A dermoscopic close-up of a skin lesion.
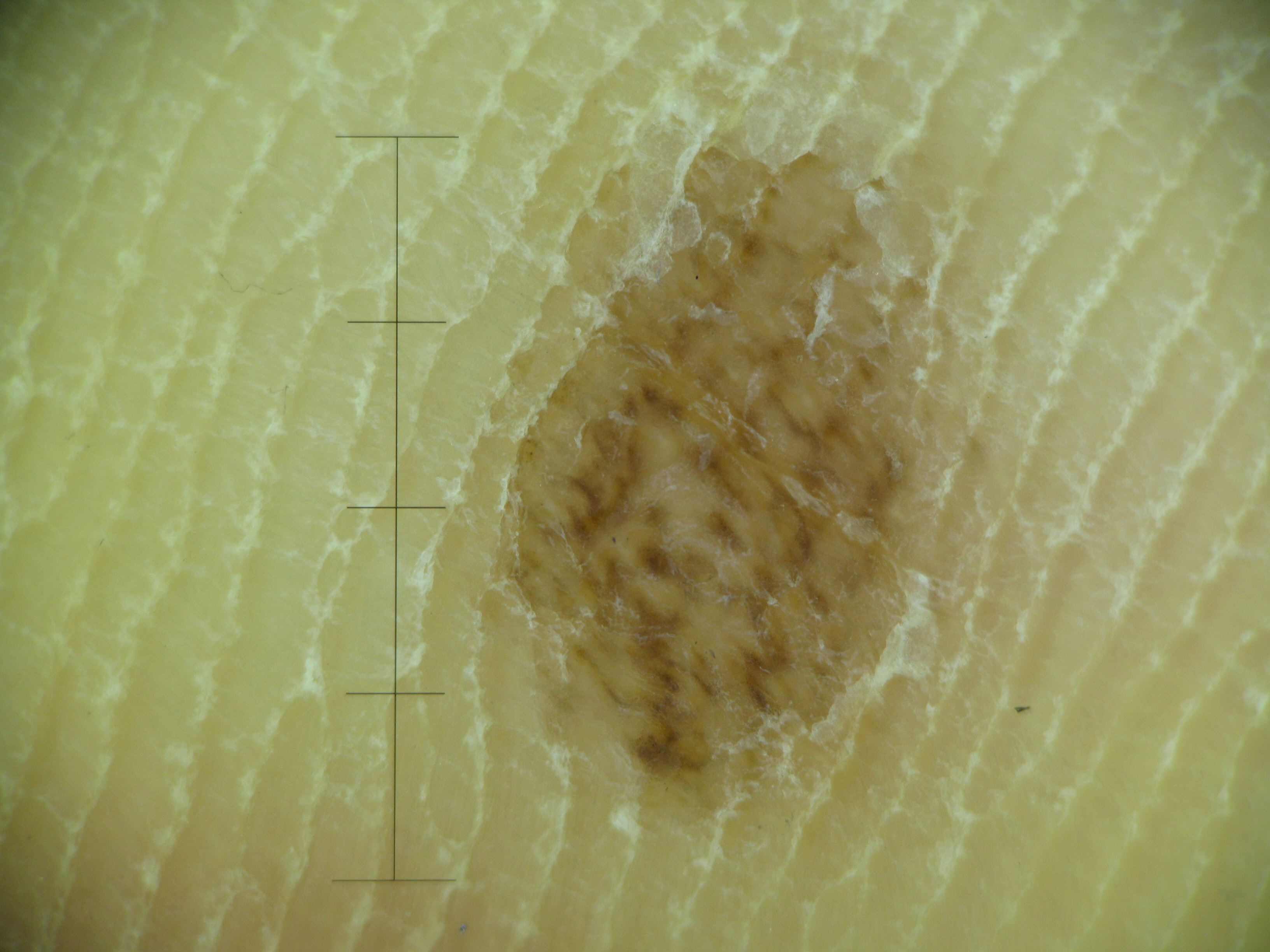{"diagnosis": {"name": "acral compound nevus", "code": "acb", "malignancy": "benign", "super_class": "melanocytic", "confirmation": "expert consensus"}}